Male patient, age 30–39. The lesion involves the leg. The photograph was taken at a distance.
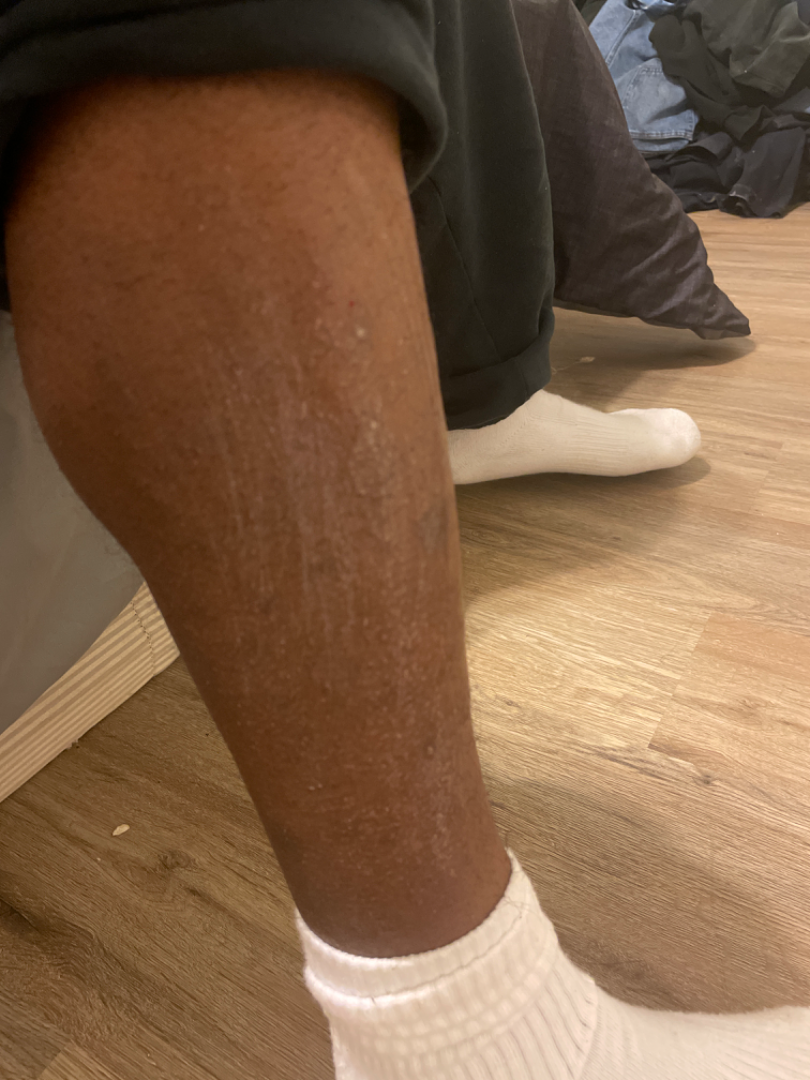The reviewing dermatologist was unable to assign a differential diagnosis from the image.
Symptoms reported: itching.
The patient indicates the lesion is rough or flaky.
The patient indicates the condition has been present for one to four weeks.